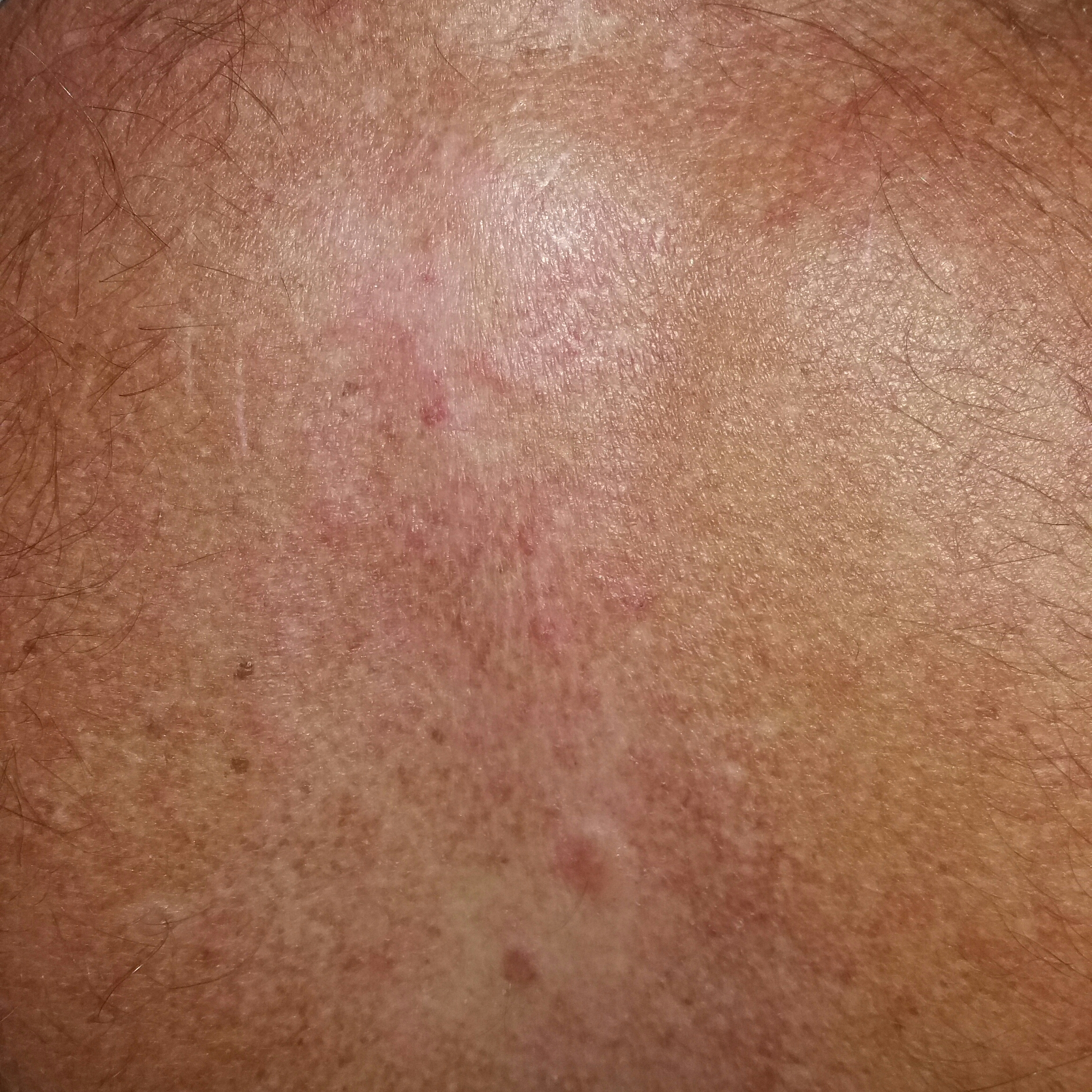A subject in their 50s.
A clinical photo of a skin lesion taken with a smartphone.
The lesion was found on the back.
Diagnosed by dermatologist consensus as an actinic keratosis.